A clinical photograph showing a skin lesion: 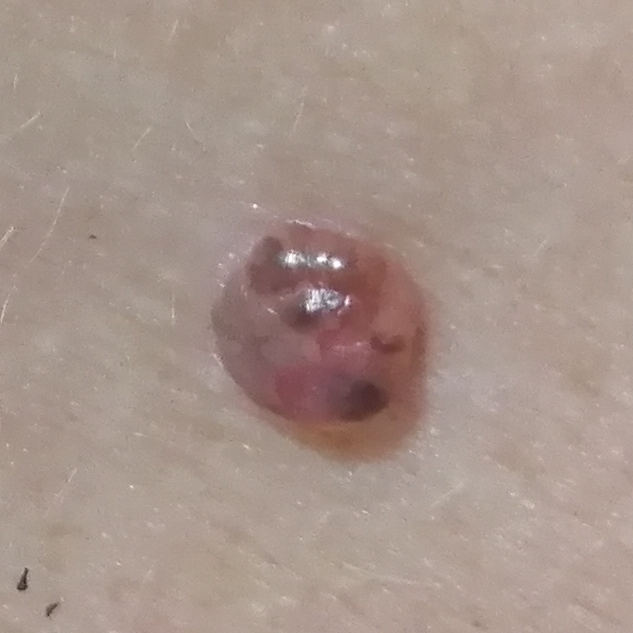patient-reported symptoms = growth, change in appearance, elevation, itching | pathology = basal cell carcinoma (biopsy-proven).